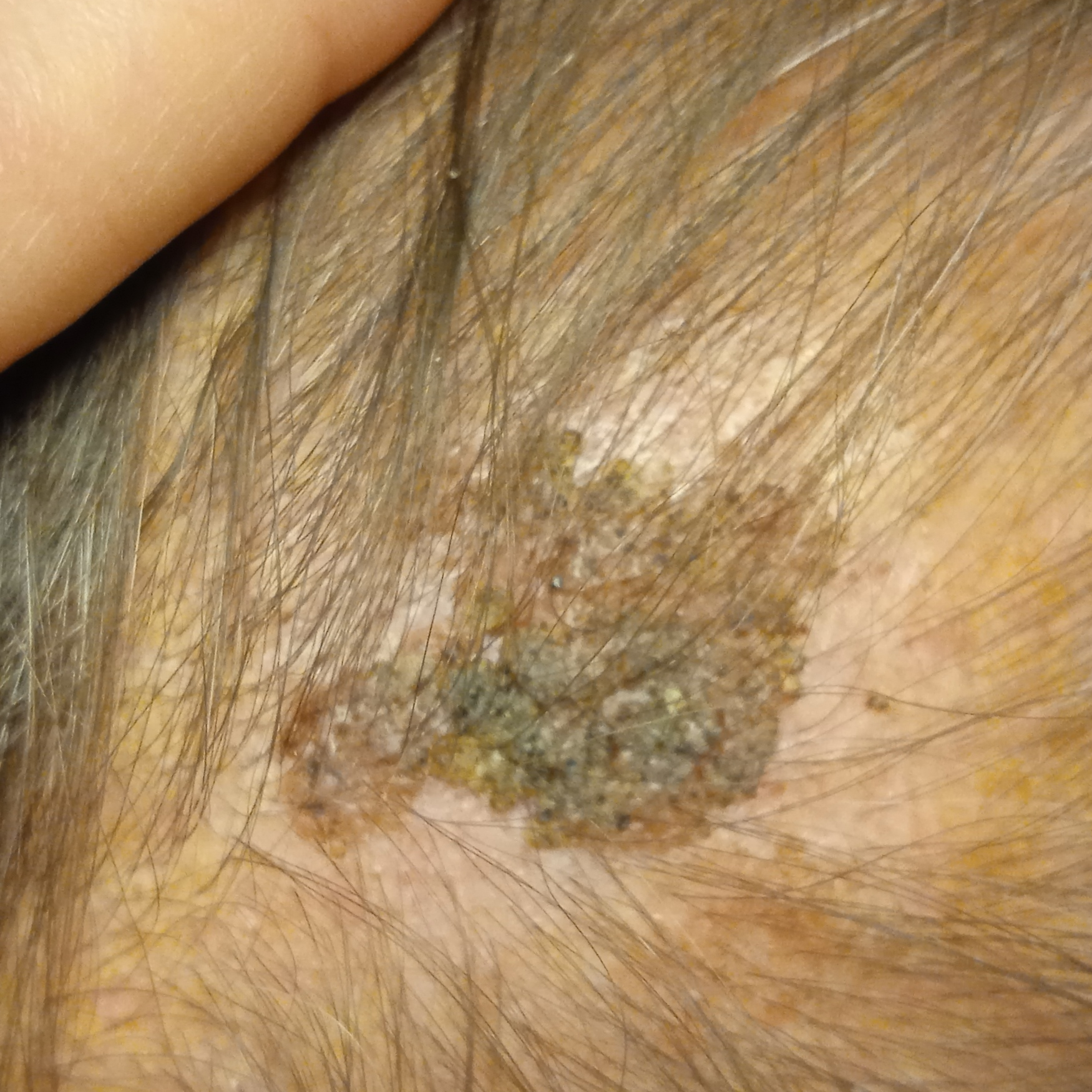Imaged for a research study, with no referral diagnosis recorded.
A male subject age 72.
A clinical photograph of a skin lesion.
The lesion is located on the head.
Measuring roughly 19.2 mm.
The lesion was assessed as a seborrheic keratosis.